A dermatoscopic image of a skin lesion.
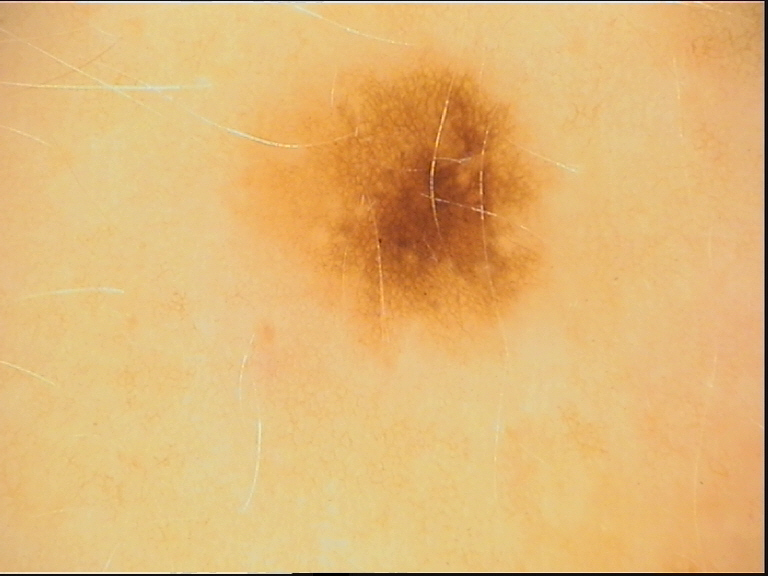  diagnosis:
    name: dysplastic junctional nevus
    code: jd
    malignancy: benign
    super_class: melanocytic
    confirmation: expert consensus